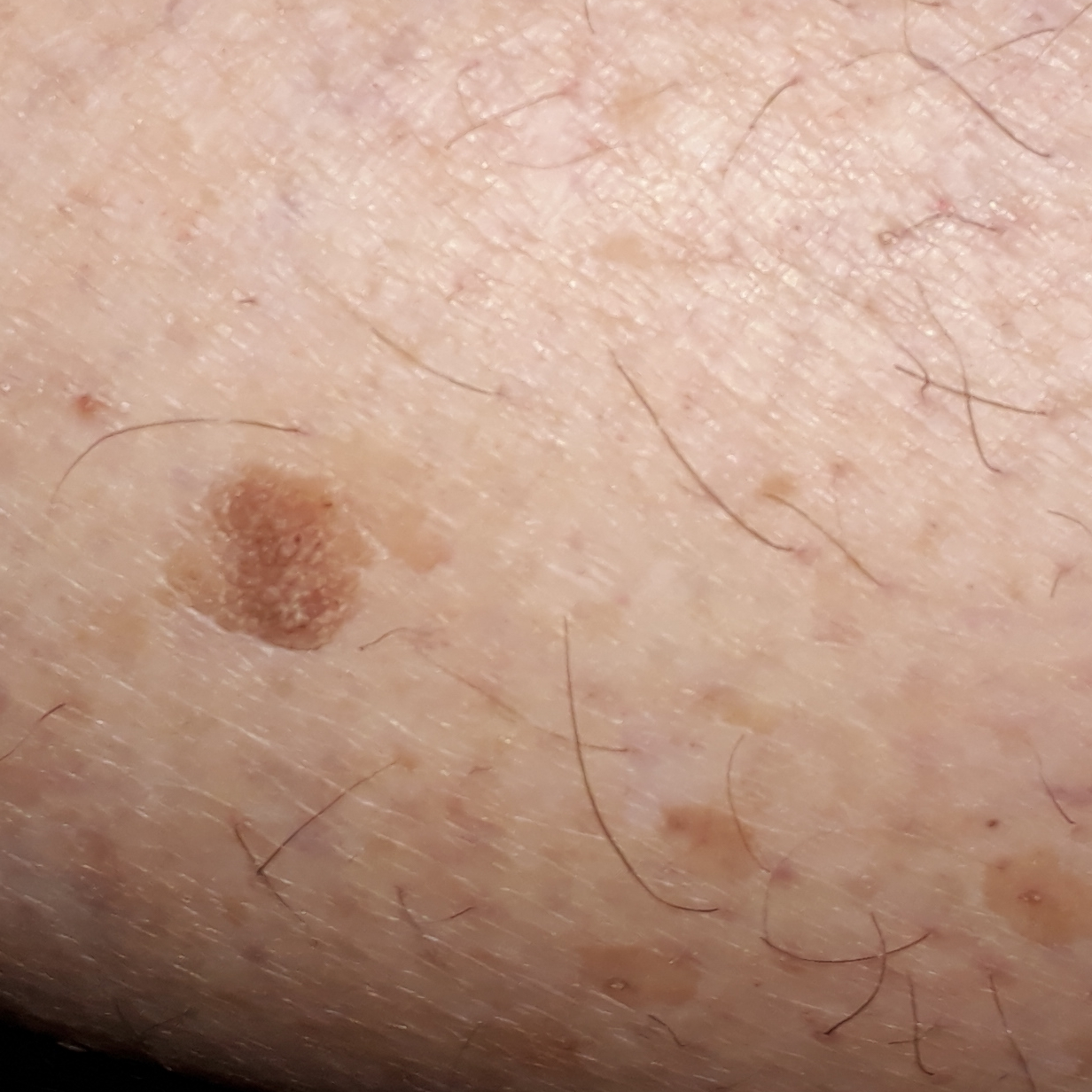The patient reports that the lesion is elevated, has grown, and itches. The consensus clinical diagnosis was a benign skin lesion — a seborrheic keratosis.